A subject 45 years old:
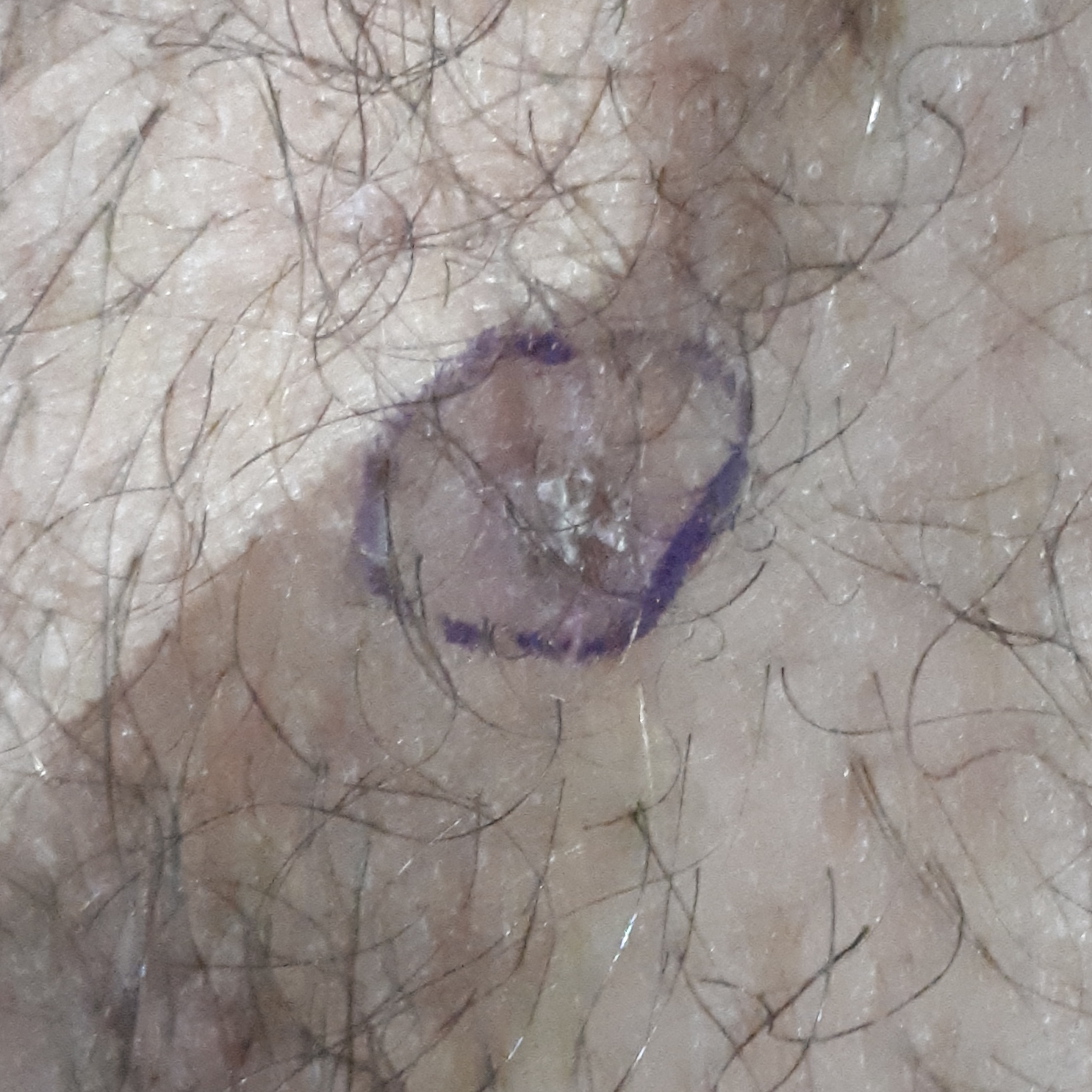Summary: The lesion involves a forearm. The patient describes that the lesion is elevated and itches. Conclusion: Diagnosed by dermatologist consensus as an actinic keratosis.